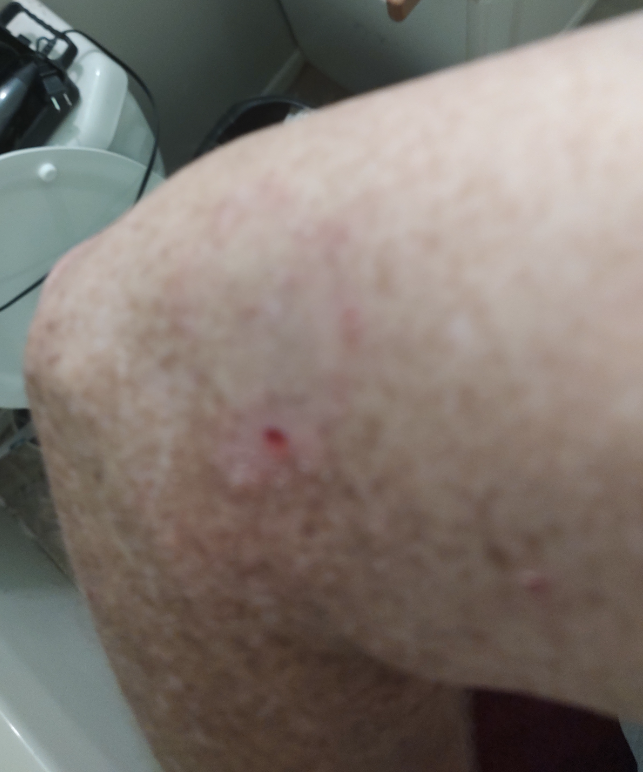The dermatologist could not determine a likely condition from the photograph alone. This image was taken at an angle.